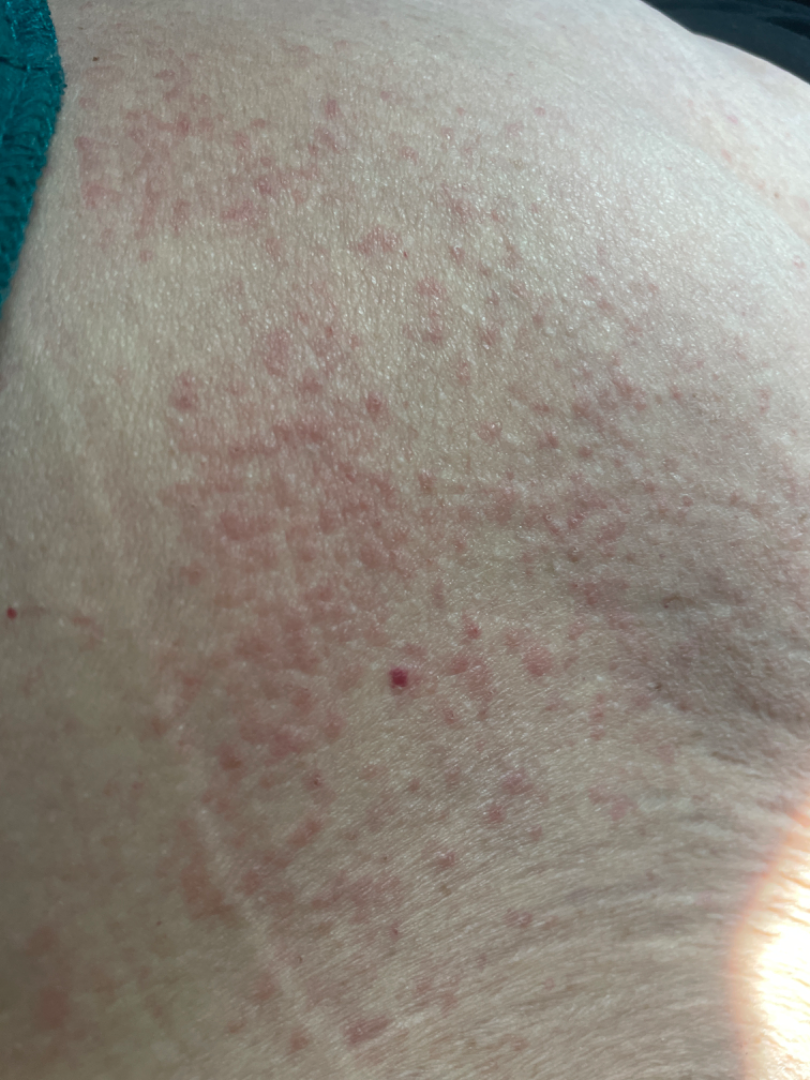{
  "patient": "female, age 50–59",
  "shot_type": "close-up",
  "body_site": "front of the torso",
  "differential": {
    "leading": [
      "Allergic Contact Dermatitis"
    ],
    "considered": [
      "Hypersensitivity"
    ],
    "unlikely": [
      "Drug Rash",
      "Eczema"
    ]
  }
}